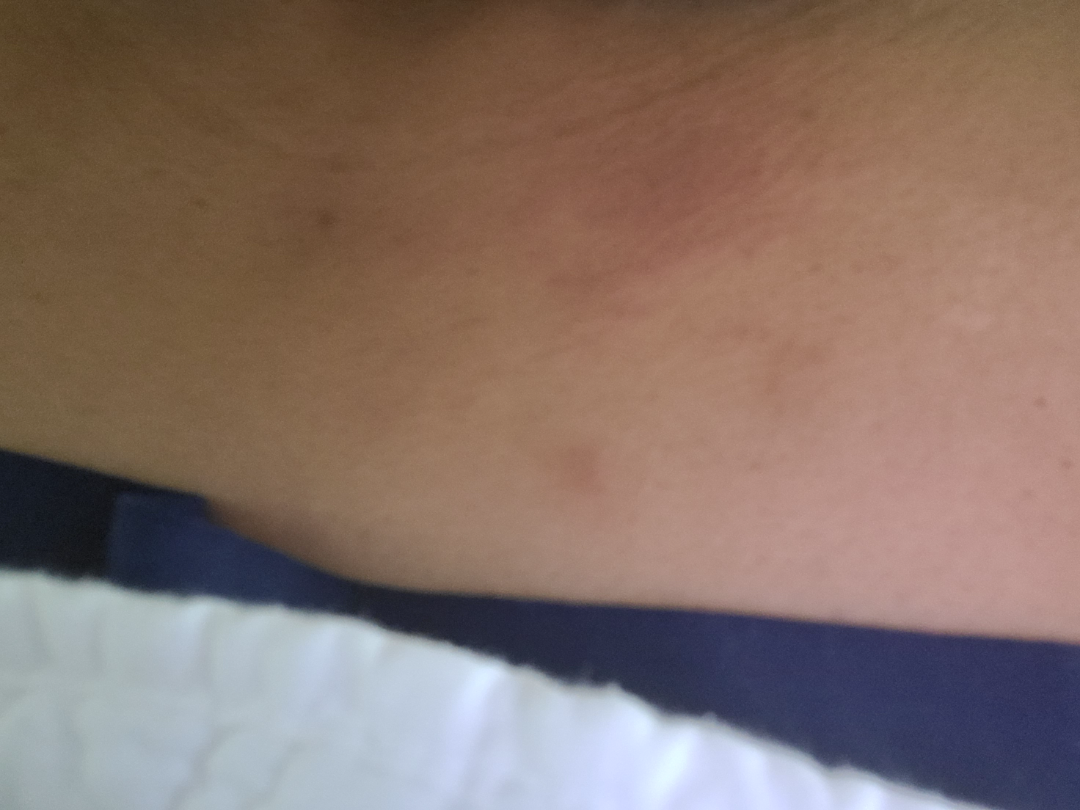{"symptoms": ["bothersome appearance", "itching"], "duration": "less than one week", "patient": "female, age 50–59", "texture": "raised or bumpy", "shot_type": "close-up", "patient_category": "a rash", "differential": {"leading": ["Urticaria"]}}